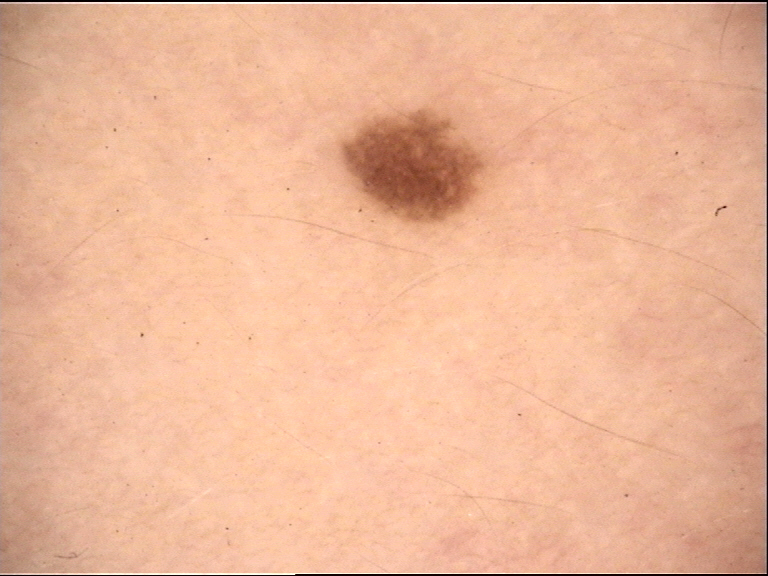Consistent with a benign lesion — a dysplastic junctional nevus.